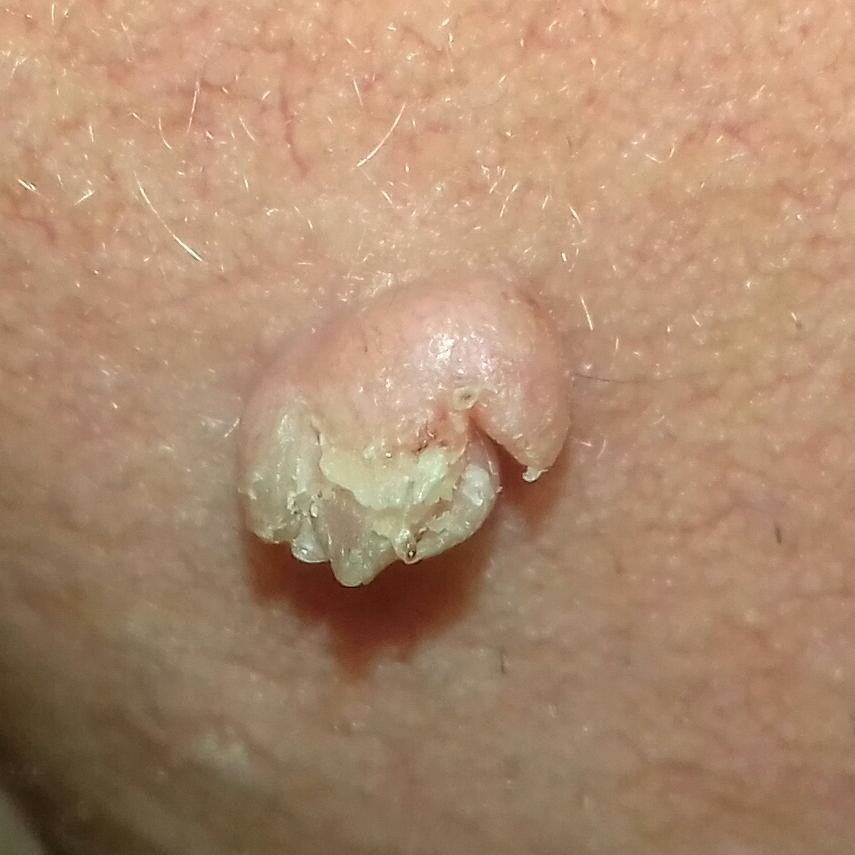<case>
<skin_type>II</skin_type>
<image>clinical photograph</image>
<patient>
<age>68</age>
<gender>male</gender>
</patient>
<lesion_location>the face</lesion_location>
<lesion_size>
<diameter_1_mm>5.0</diameter_1_mm>
<diameter_2_mm>3.0</diameter_2_mm>
</lesion_size>
<symptoms>
<present>itching, growth, elevation</present>
</symptoms>
<diagnosis>
<name>actinic keratosis</name>
<code>ACK</code>
<malignancy>indeterminate</malignancy>
<confirmation>histopathology</confirmation>
</diagnosis>
</case>